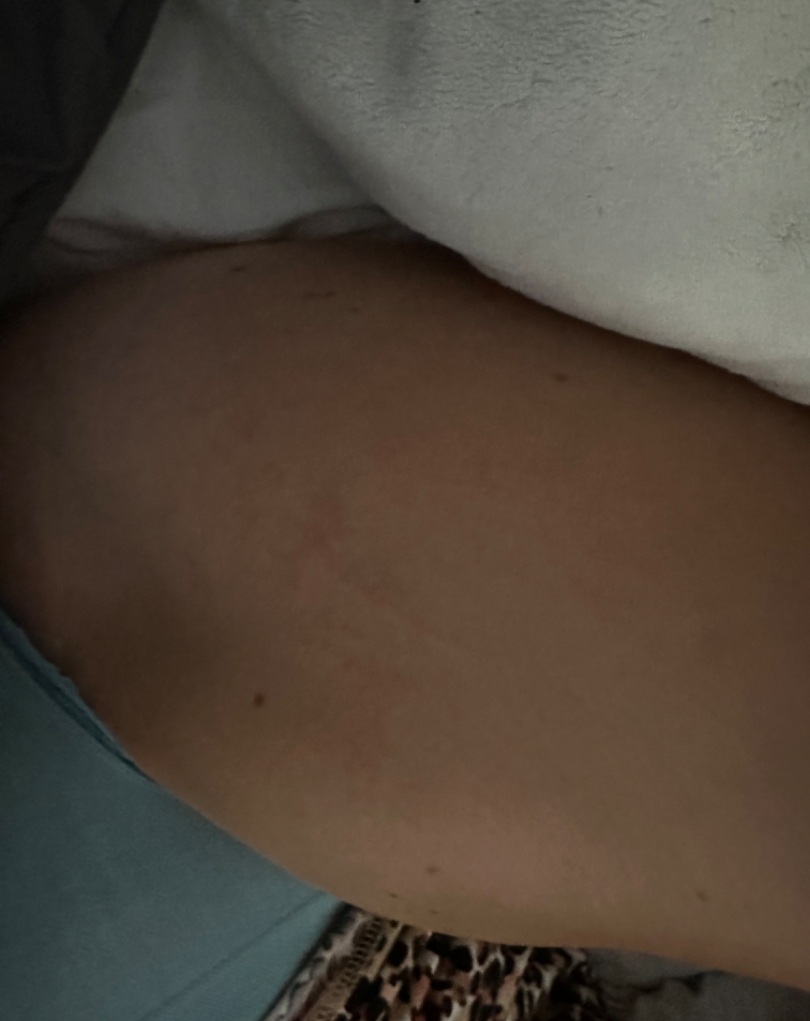The case was difficult to assess from the available photograph.